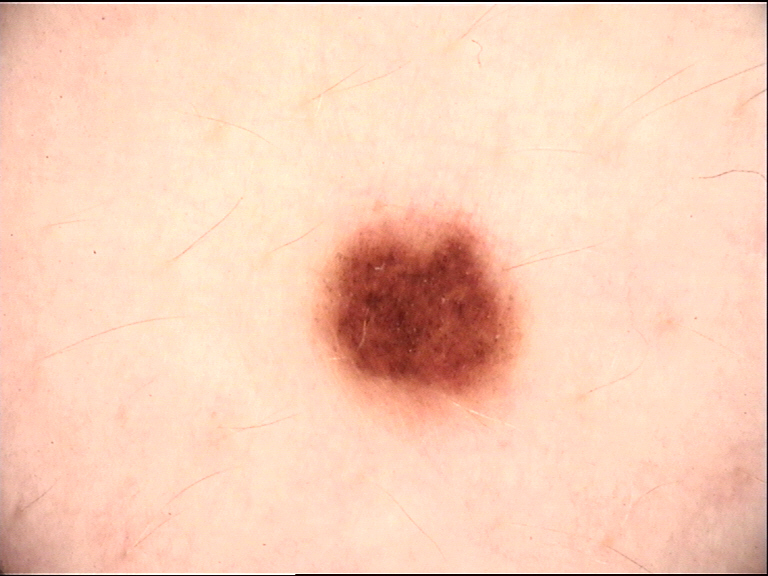Findings:
A dermoscopic image of a skin lesion. The architecture is that of a banal lesion.
Conclusion:
Consistent with a junctional nevus.